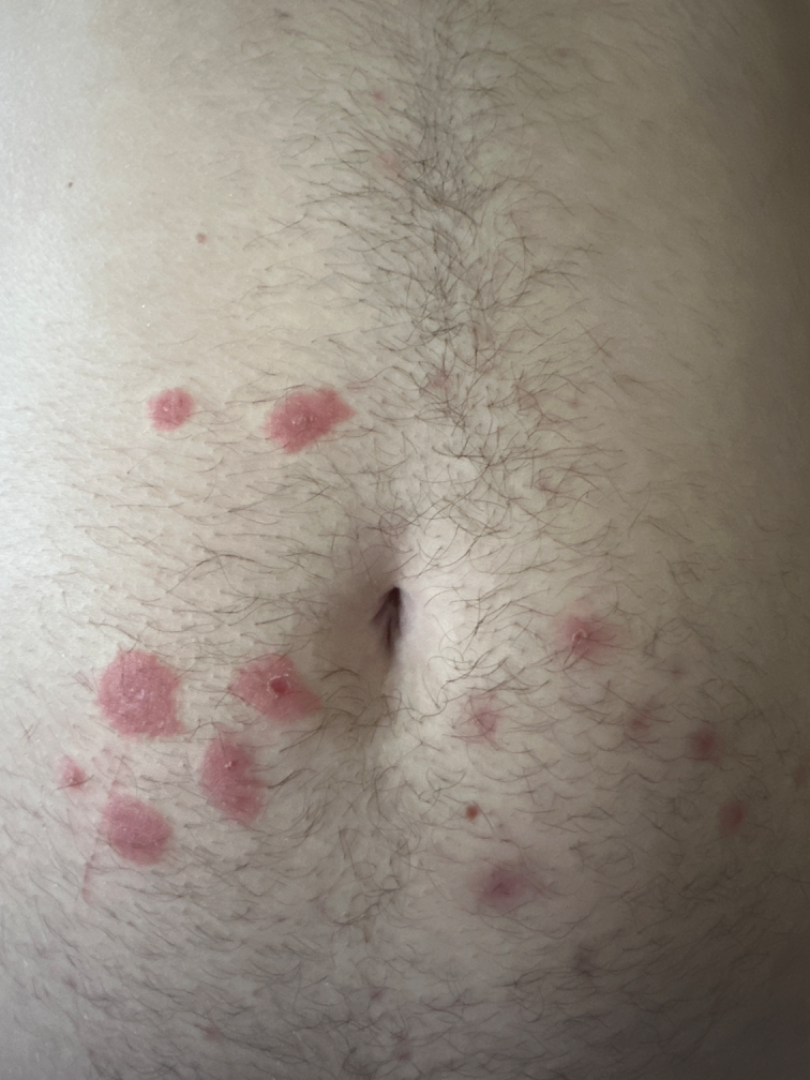Notes:
* view · close-up
* texture · raised or bumpy
* affected area · front of the torso
* skin tone · FST II; human graders estimated a MST of 2
* onset · one to four weeks
* dermatologist impression · most likely Insect Bite; also on the differential is Sweet syndrome